A clinical photograph showing a skin lesion; recorded as FST II — 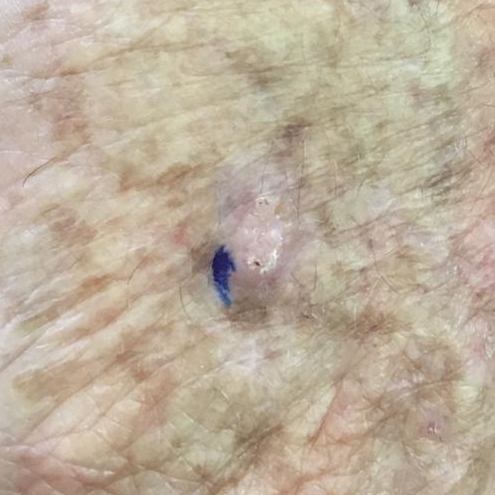Q: What is the anatomic site?
A: a hand
Q: What symptoms does the patient report?
A: itching
Q: What did the workup show?
A: actinic keratosis (biopsy-proven)